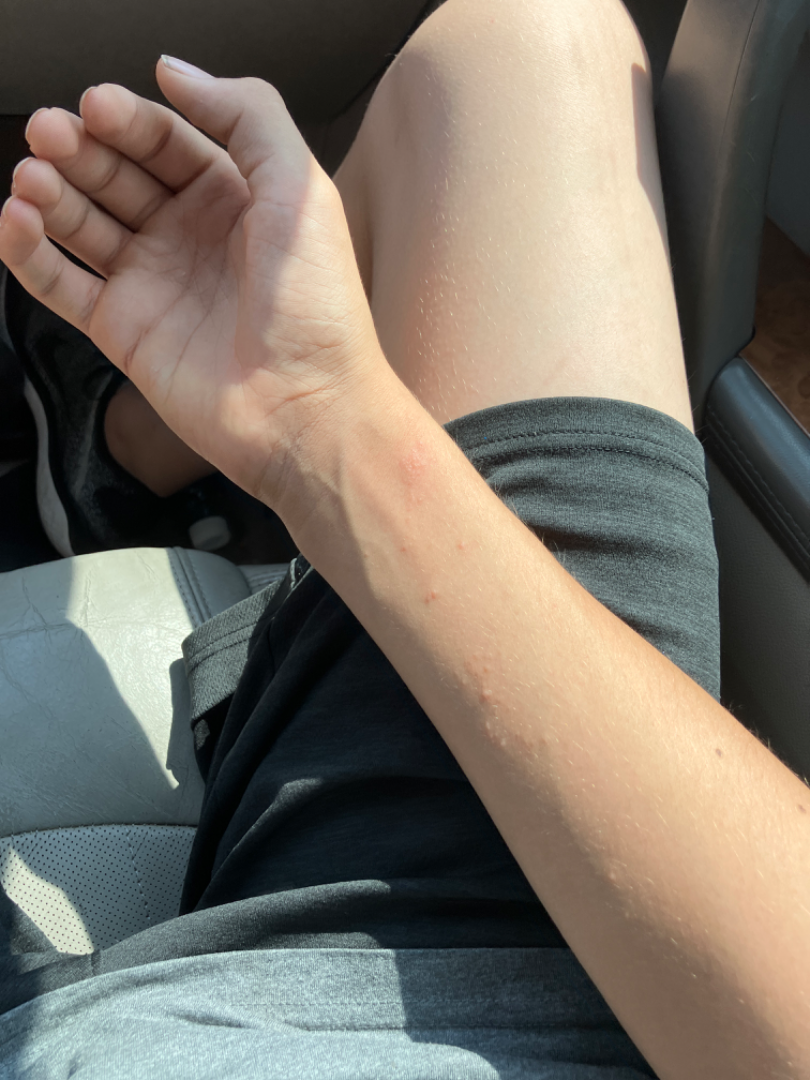Patient information:
The lesion involves the arm. This image was taken at a distance.
Review:
Allergic Contact Dermatitis (weight 0.57); Eczema (weight 0.36); Insect Bite (weight 0.07).